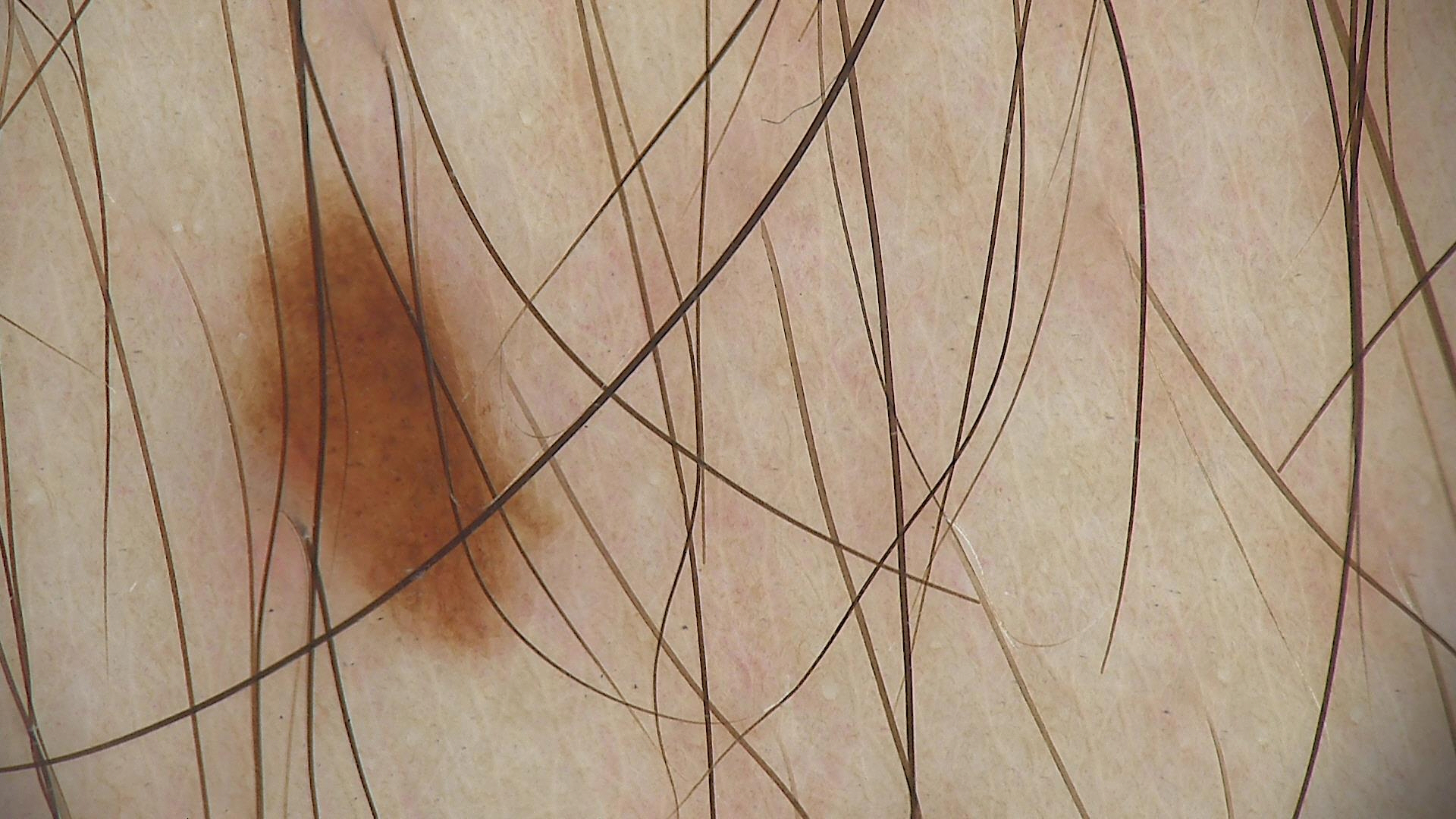A dermatoscopic image of a skin lesion.
Diagnosed as a dysplastic junctional nevus.